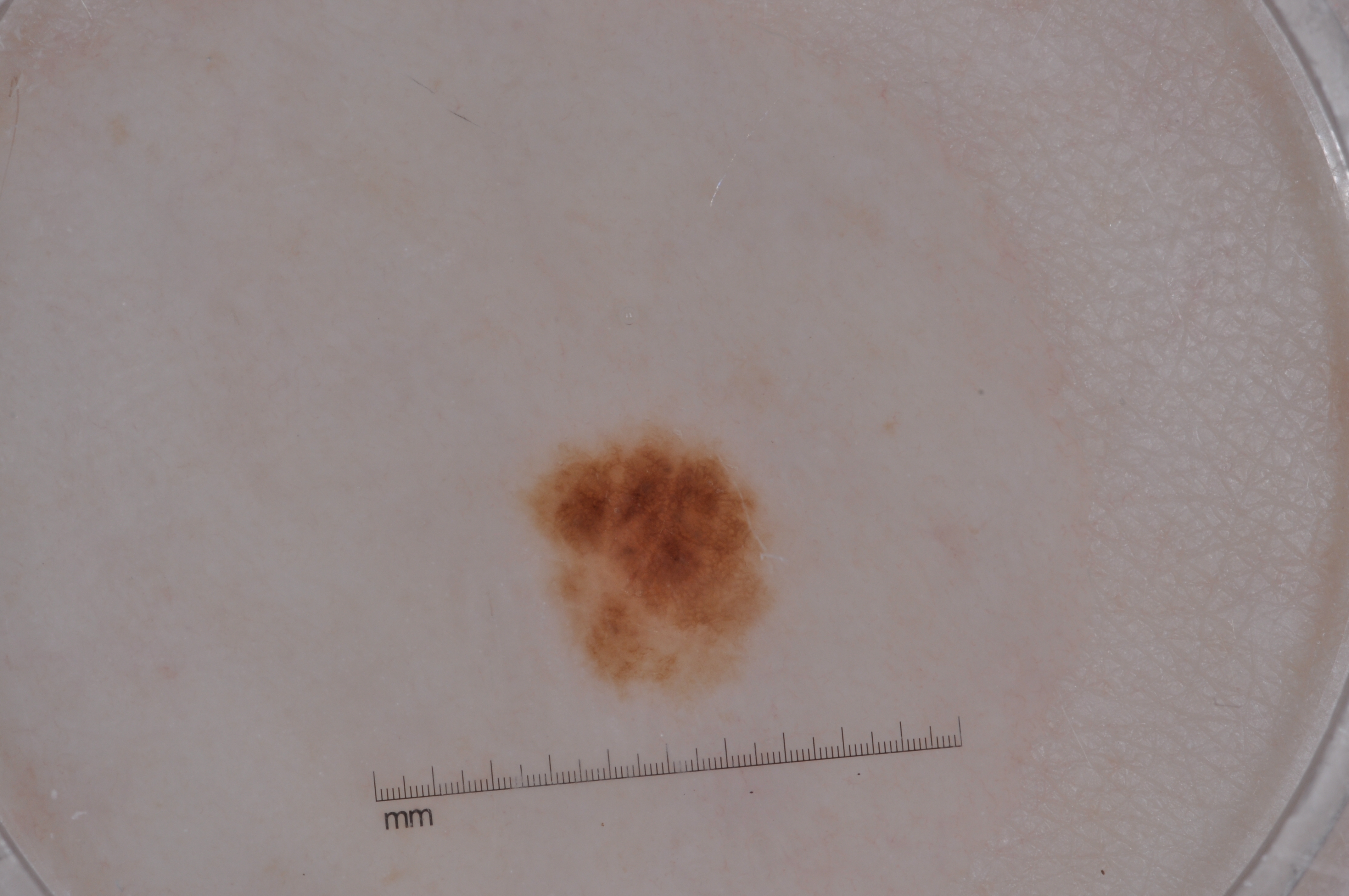Dermoscopy of a skin lesion. With coordinates (x1, y1, x2, y2), the lesion spans (527, 427, 769, 693). The clinical diagnosis was a melanocytic nevus, a benign lesion.